A female patient approximately 70 years of age. An overview clinical photograph of a skin lesion — 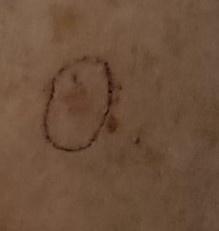Histopathological examination showed a squamous cell carcinoma.